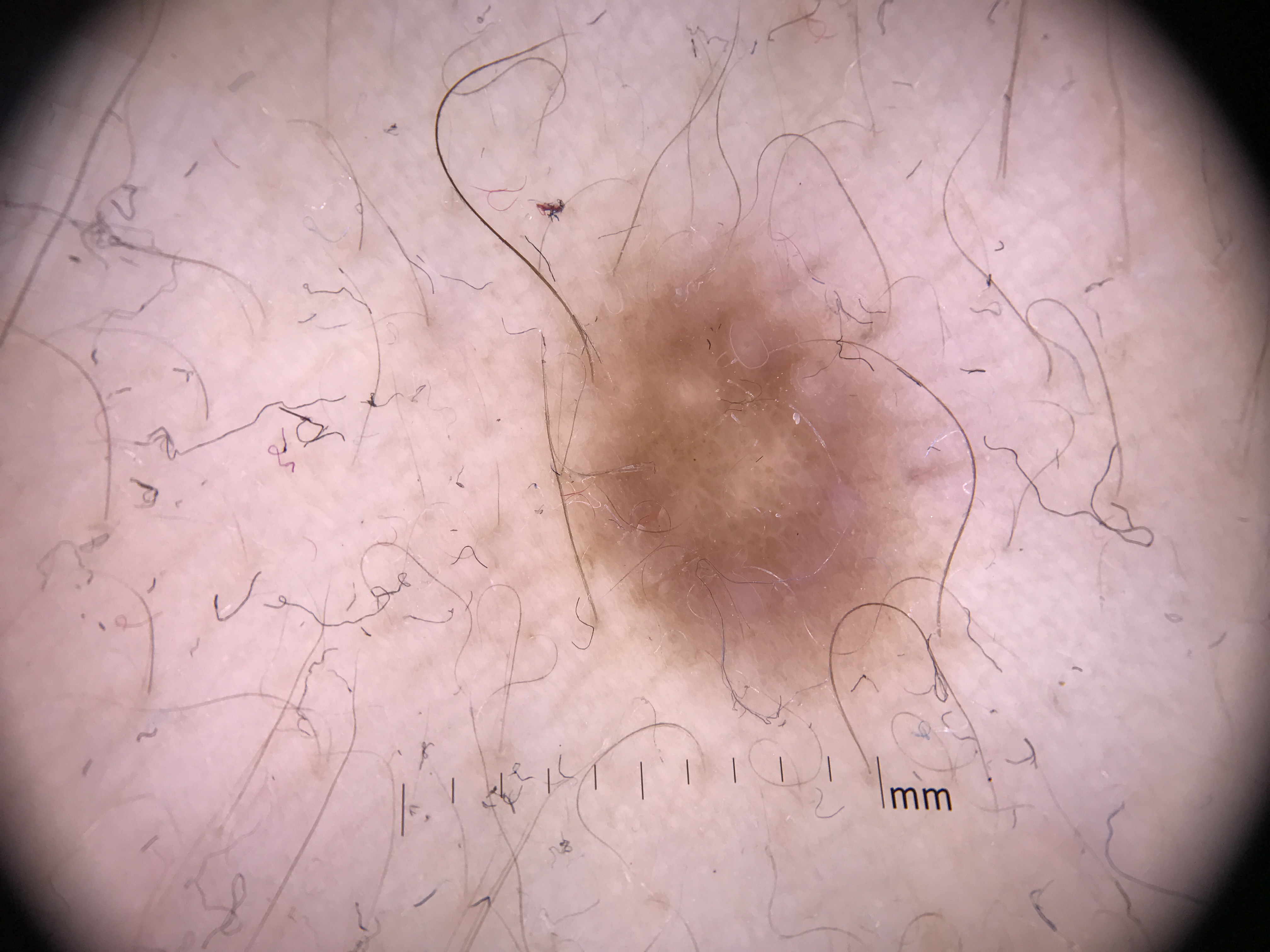– label — dermatofibroma (expert consensus)